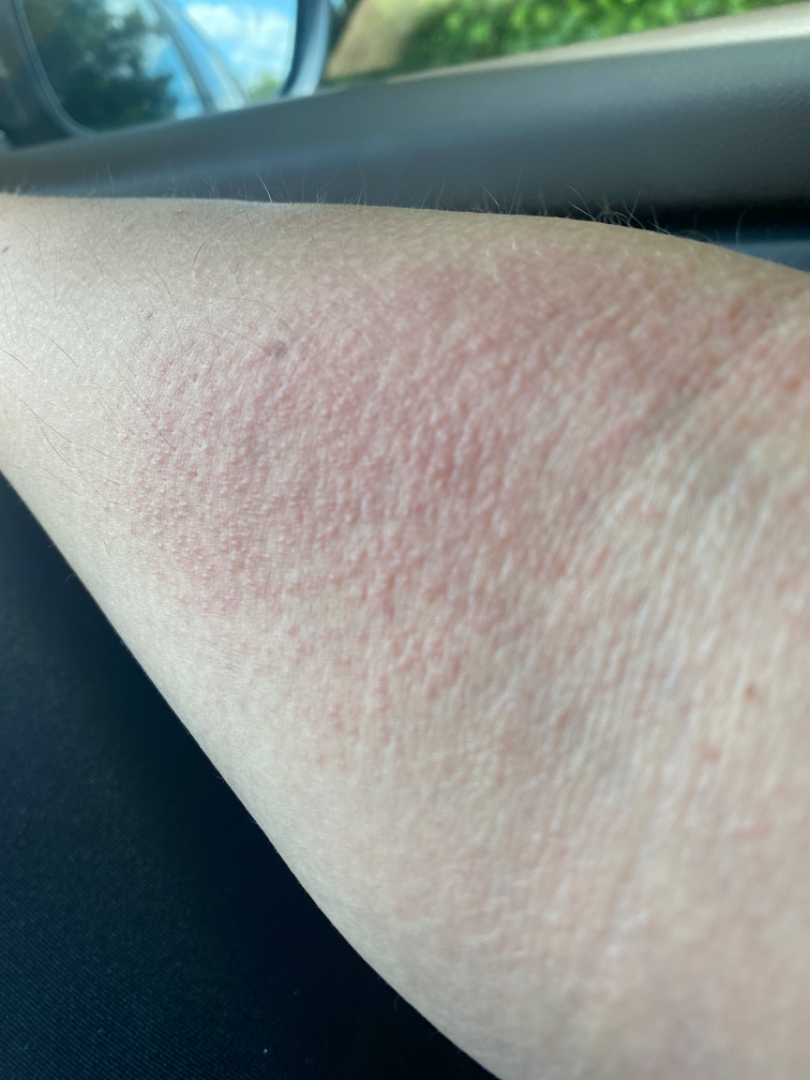Findings:
On teledermatology review: Eczema and Allergic Contact Dermatitis were considered with similar weight.